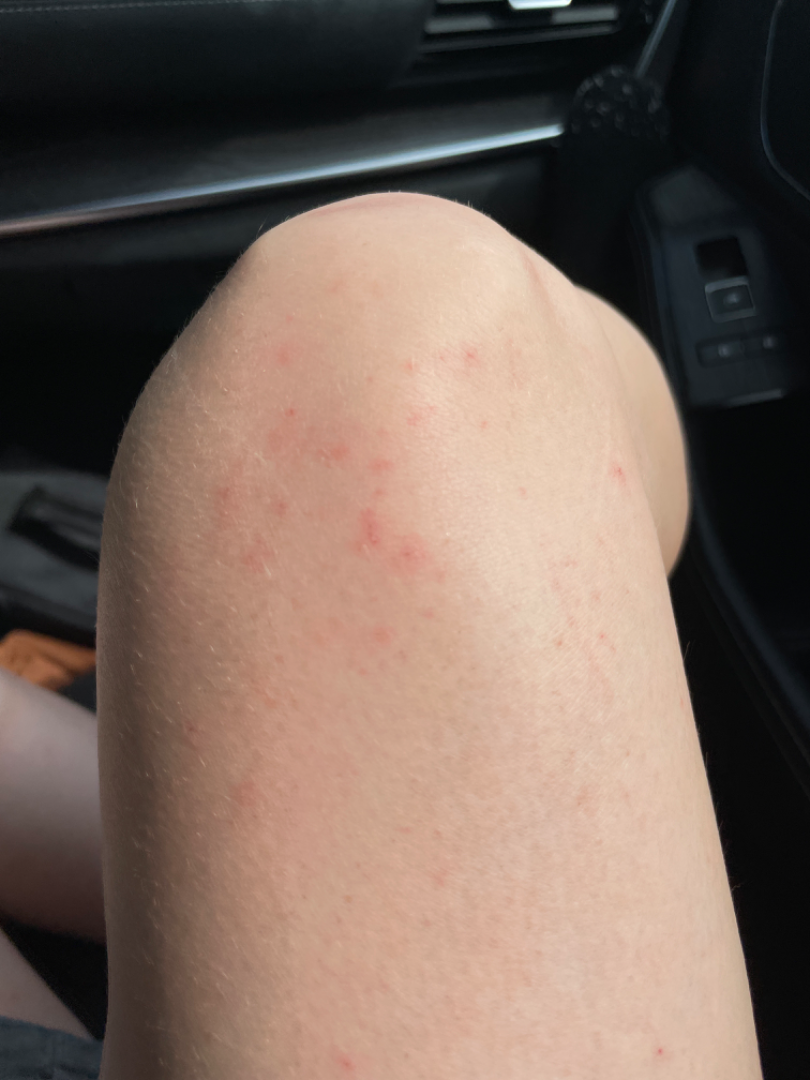Clinical context:
The leg is involved. The patient is a female aged 18–29. This is a close-up image.
Assessment:
On photographic review: favoring Folliculitis; the differential also includes Eczema.